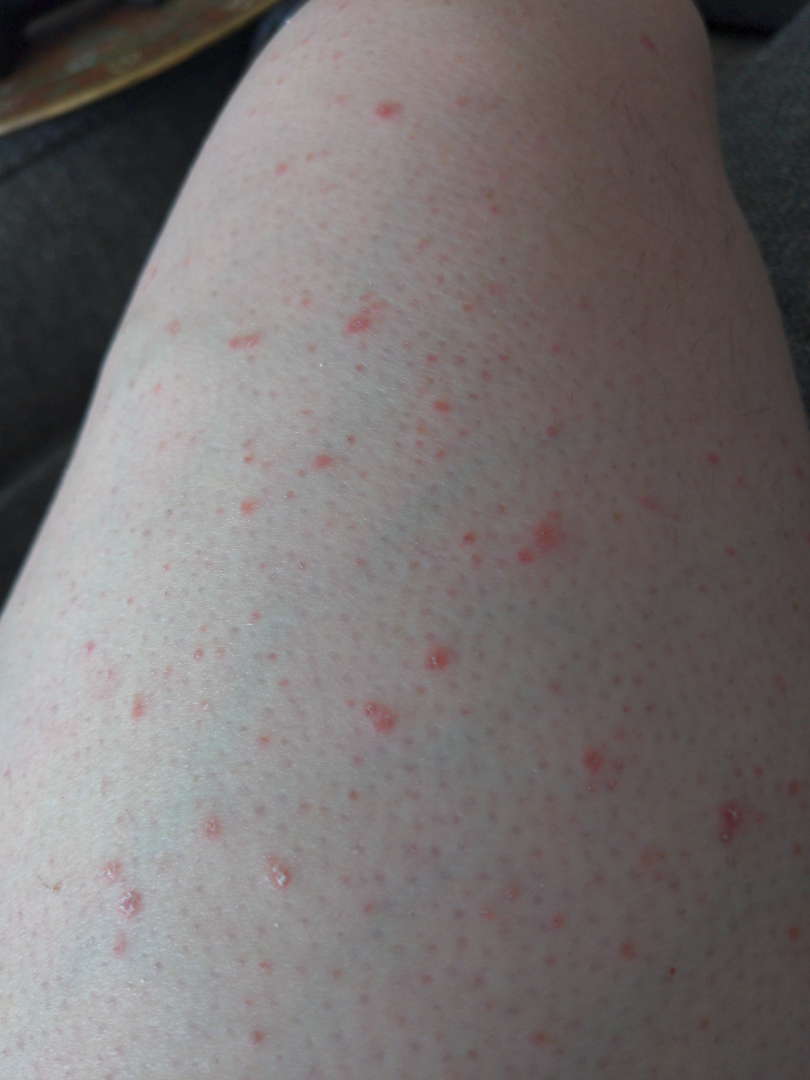| field | value |
|---|---|
| lesion symptoms | itching and bothersome appearance |
| patient describes the issue as | a rash |
| framing | close-up |
| body site | back of the hand, arm and leg |
| duration | one to four weeks |
| described texture | flat and rough or flaky |
| diagnostic considerations | Folliculitis (weight 0.67); Porokeratosis (weight 0.33) |